A dermoscopic view of a skin lesion — 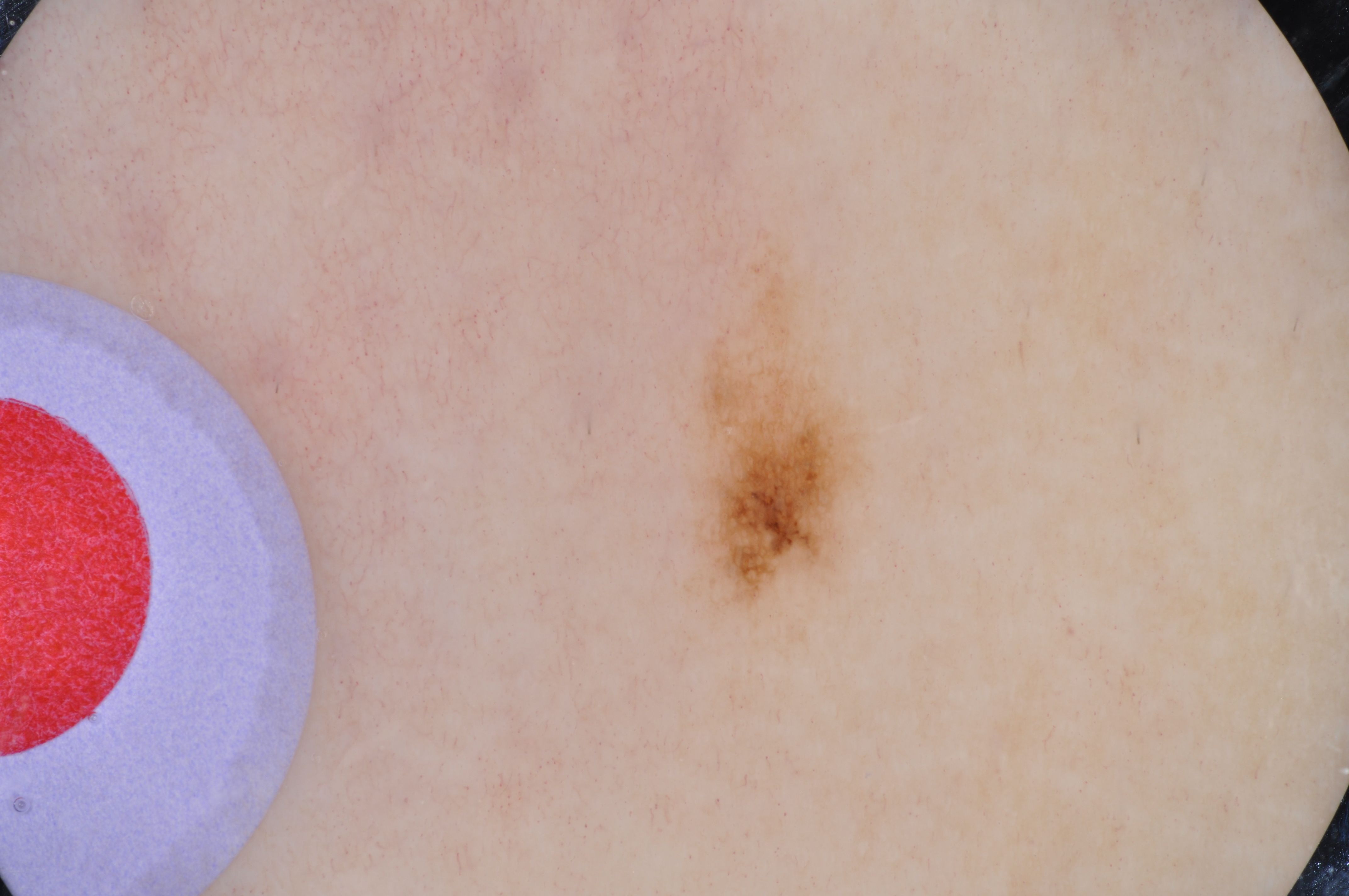  lesion_location:
    bbox_xyxy:
      - 676
      - 232
      - 873
      - 631
  dermoscopic_features:
    present:
      - pigment network
    absent:
      - negative network
      - milia-like cysts
      - streaks
      - globules
  diagnosis:
    name: melanocytic nevus
    malignancy: benign
    lineage: melanocytic
    provenance: clinical